Dermoscopy of a skin lesion:
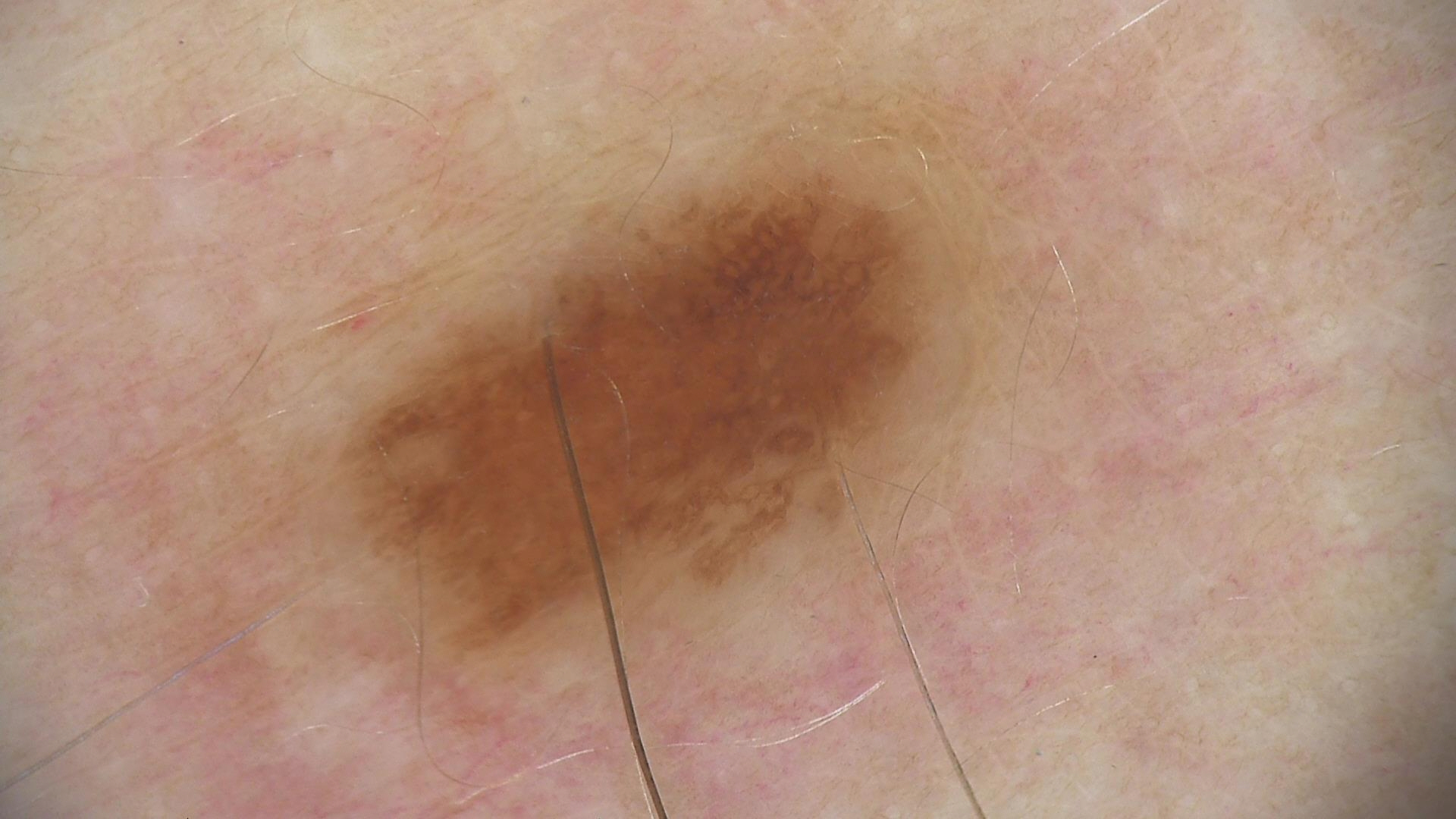diagnosis = dysplastic junctional nevus (expert consensus).